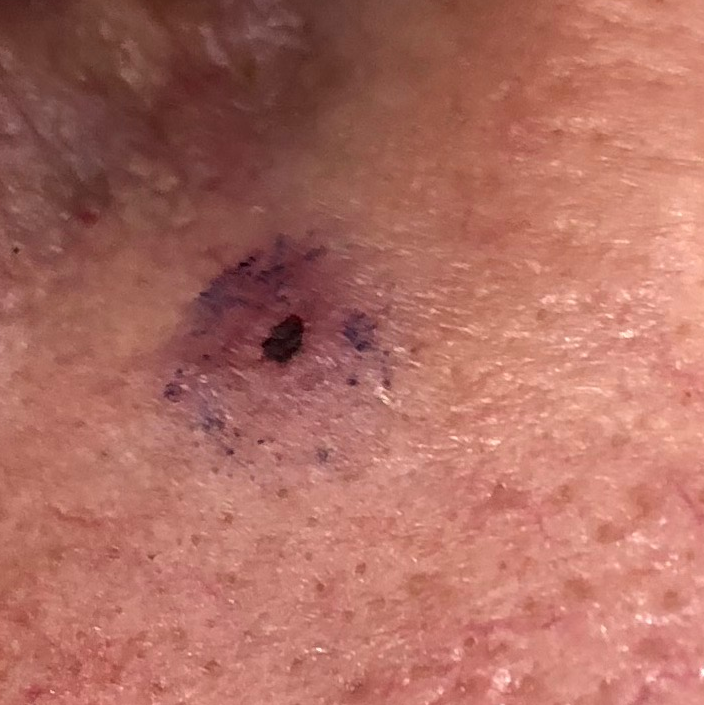Clinical context: The chart records pesticide exposure, prior malignancy (patient or family), prior skin cancer (patient or family), no tobacco use, and no alcohol use. The lesion is located on the nose. The lesion is roughly 7 by 7 mm. Per patient report, the lesion is elevated, has grown, has bled, itches, and hurts. Conclusion: Histopathological examination showed a malignant lesion — a basal cell carcinoma.